A dermoscopic image of a skin lesion:
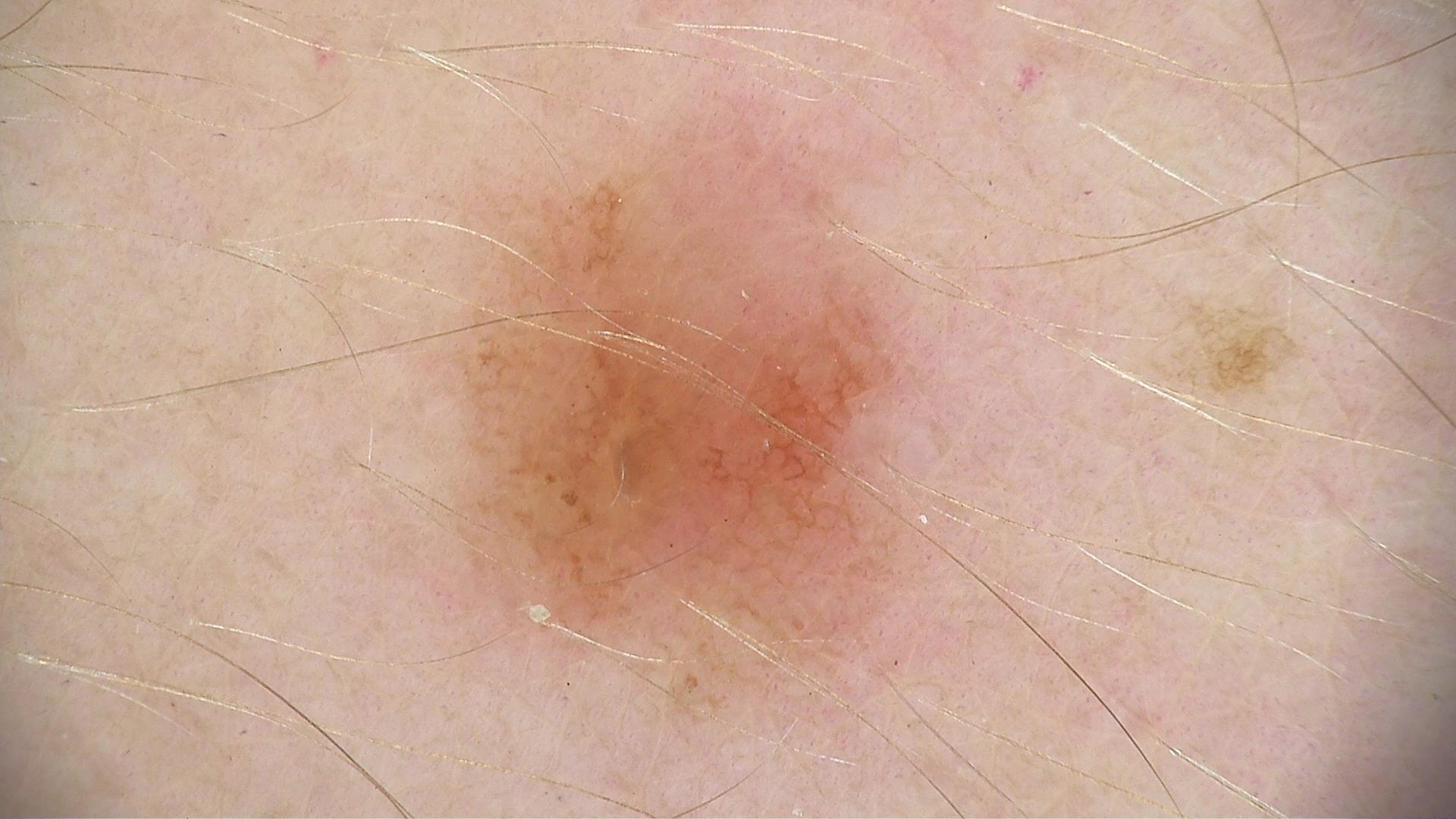assessment = dysplastic junctional nevus (expert consensus).